A clinical photograph of a skin lesion:
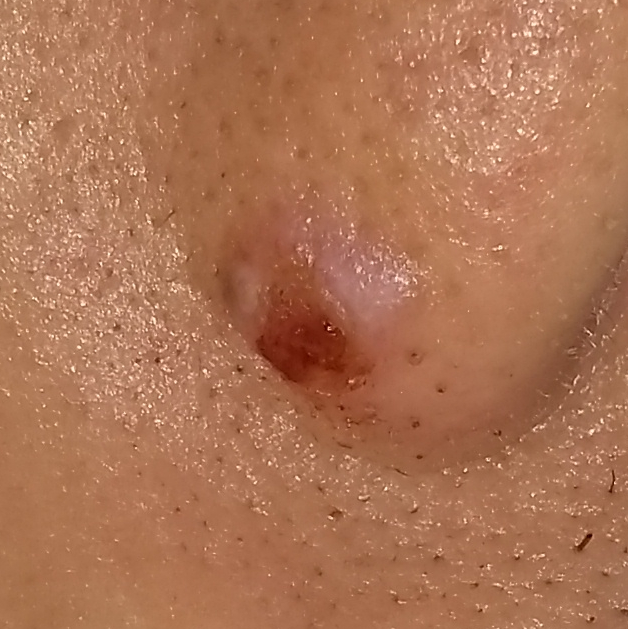The lesion involves the nose. The patient reports that the lesion has bled, itches, hurts, has grown, and is elevated, but has not changed. Histopathological examination showed a basal cell carcinoma.